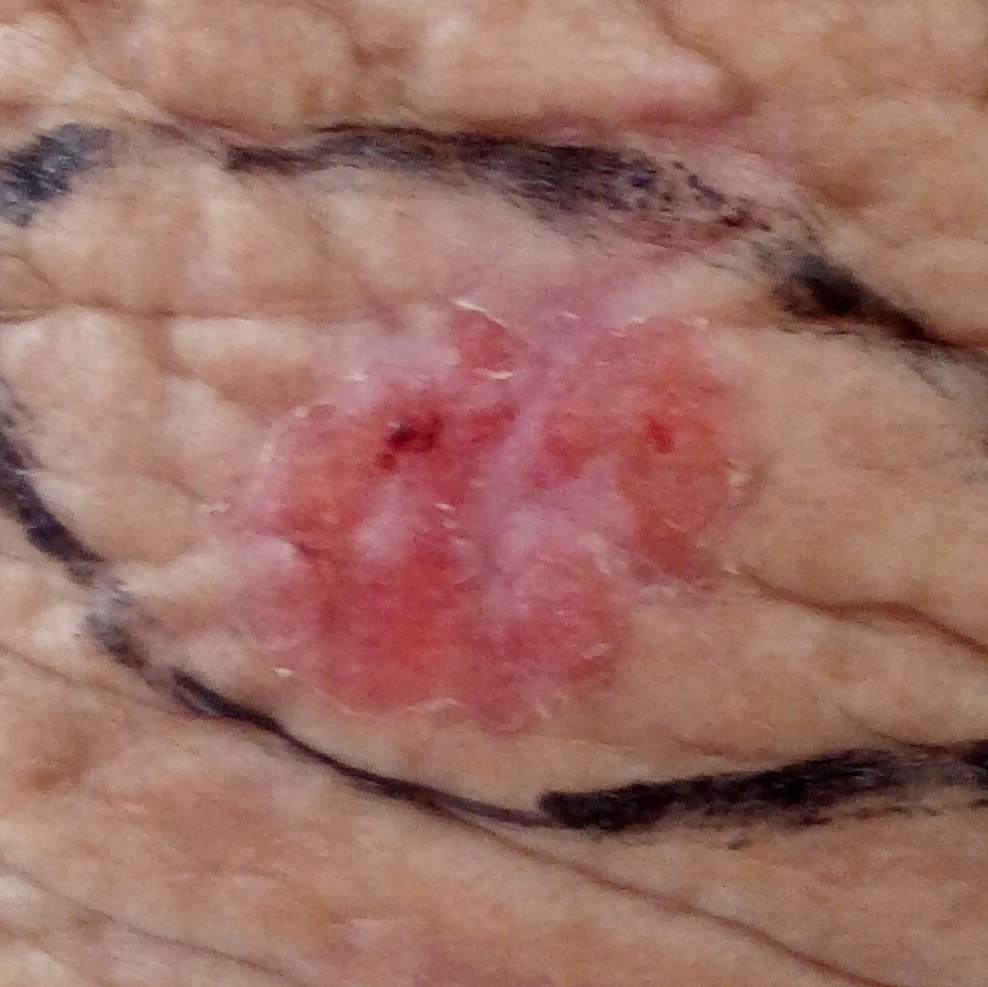A clinical photograph showing a skin lesion.
The patient describes that the lesion itches and has bled.
Histopathological examination showed a squamous cell carcinoma.